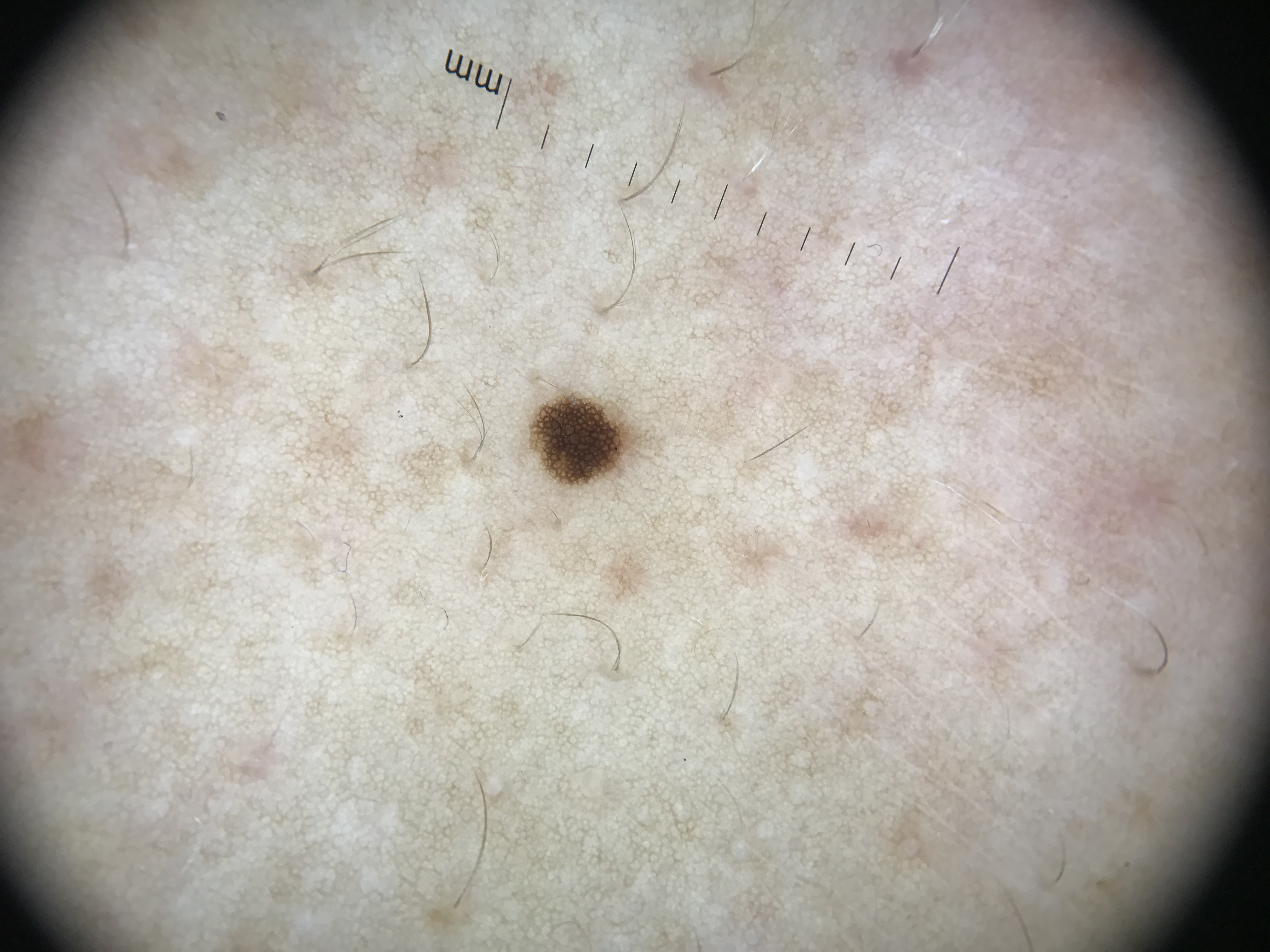  image: dermatoscopy
  lesion_type:
    main_class: banal
    pattern: junctional
  diagnosis:
    name: junctional nevus
    code: jb
    malignancy: benign
    super_class: melanocytic
    confirmation: expert consensus